The photo was captured at a distance:
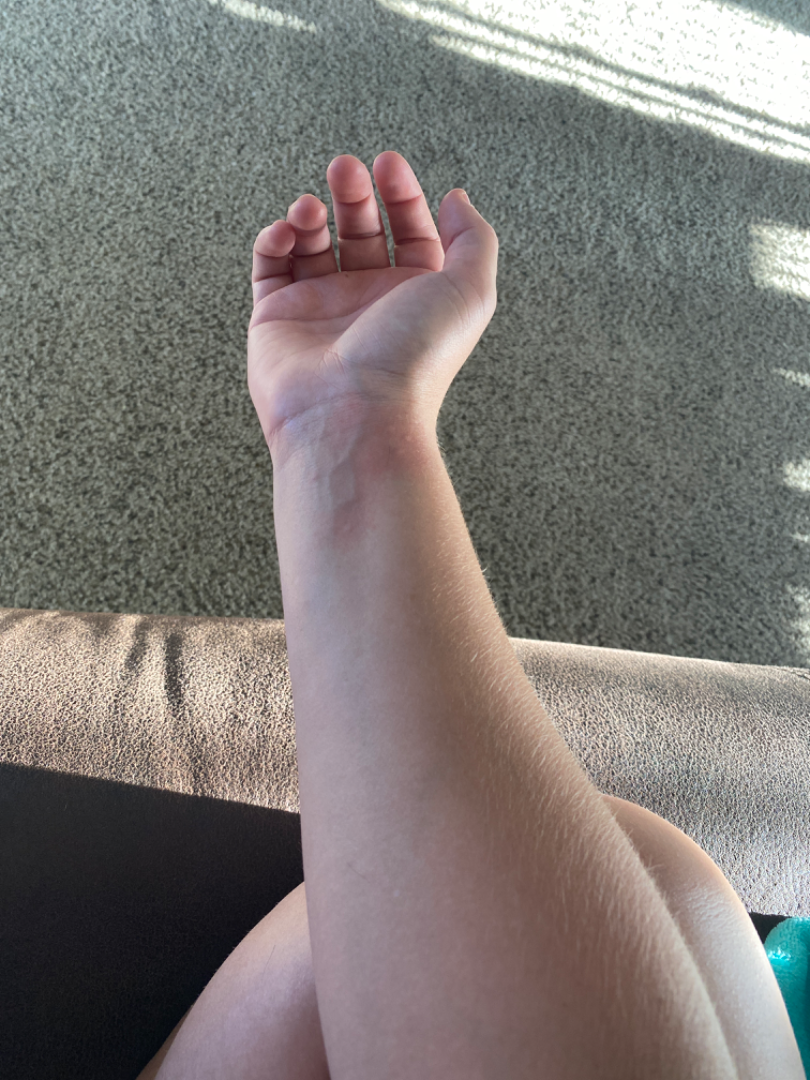Notes:
• impression: Insect Bite (most likely); Urticaria (considered)